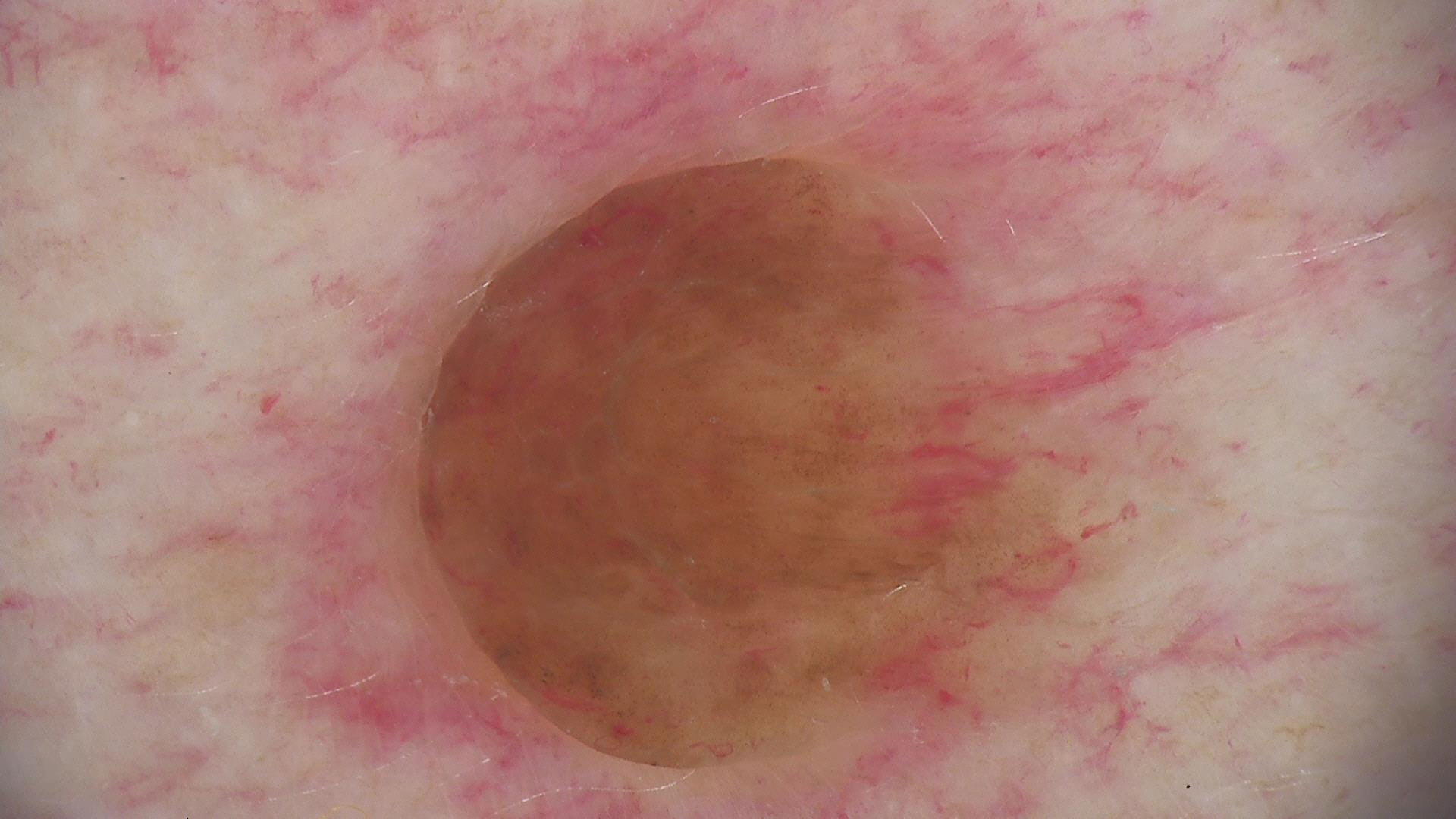lesion type: banal, label: dermal nevus (expert consensus).